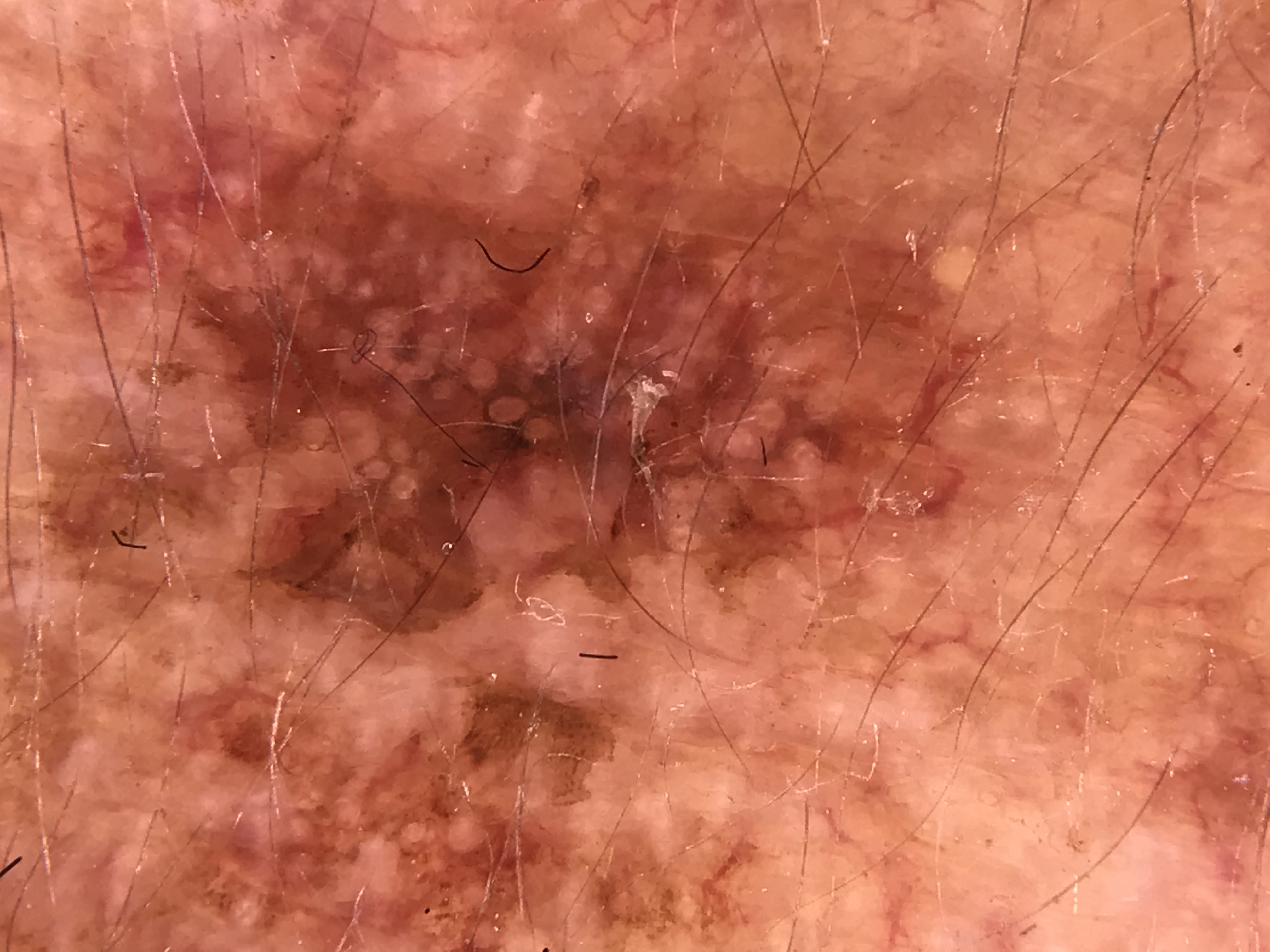Findings:
* class · actinic keratosis (expert consensus)